The patient considered this a rash; the contributor notes the condition has been present for less than one week; female patient, age 60–69; symptoms reported: itching; texture is reported as raised or bumpy; an image taken at a distance; the affected area is the arm — 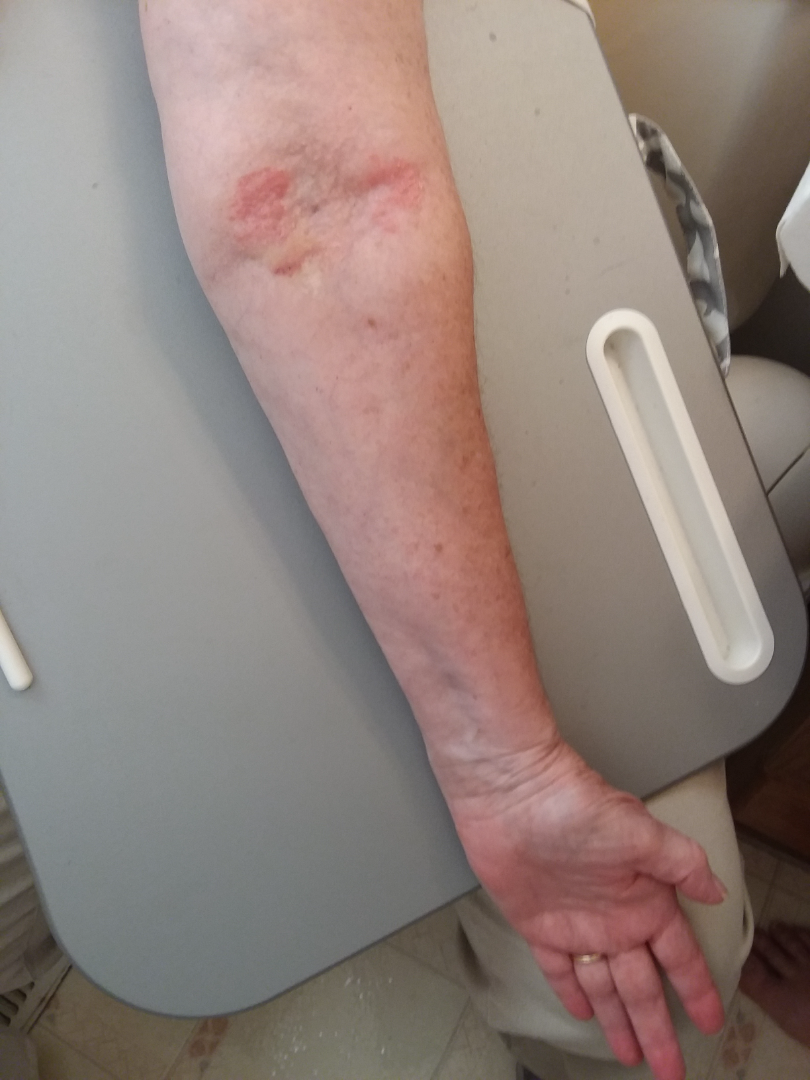assessment = unable to determine.